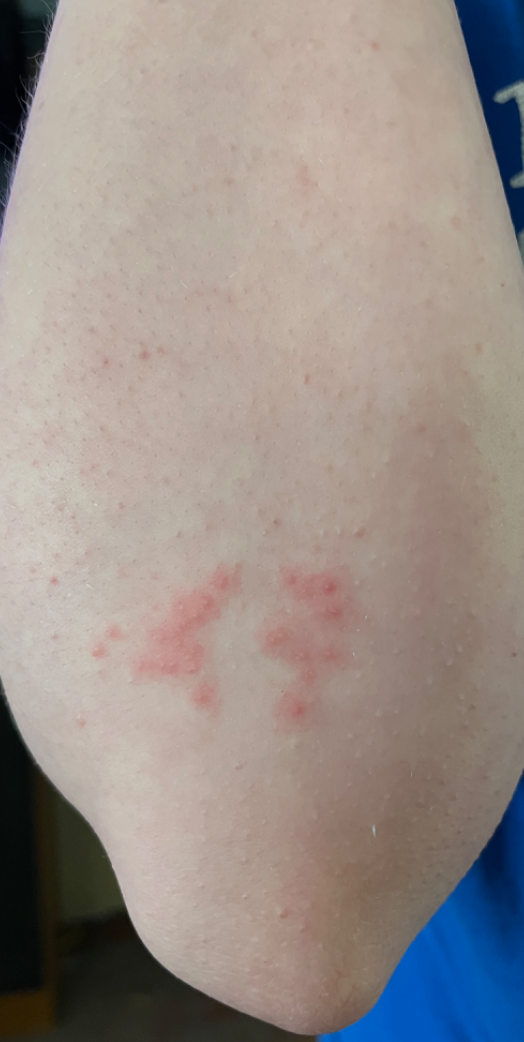assessment = indeterminate
skin tone = Fitzpatrick phototype II; human graders estimated a MST of 2
view = close-up